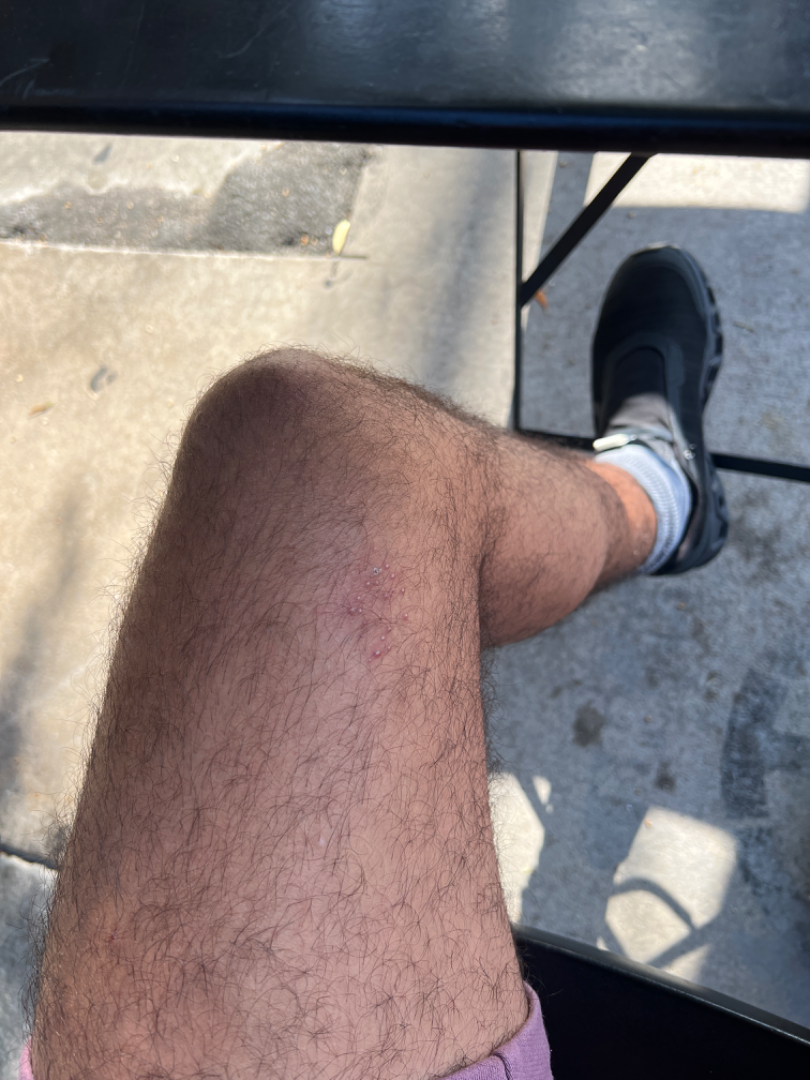systemic_symptoms: none reported
texture: raised or bumpy
body_site: leg
shot_type: at a distance
duration: less than one week
skin_tone:
  fitzpatrick: IV
  monk_skin_tone:
    - 2
    - 4
symptoms: bothersome appearance
differential:
  leading:
    - Herpes Simplex
  considered:
    - Folliculitis